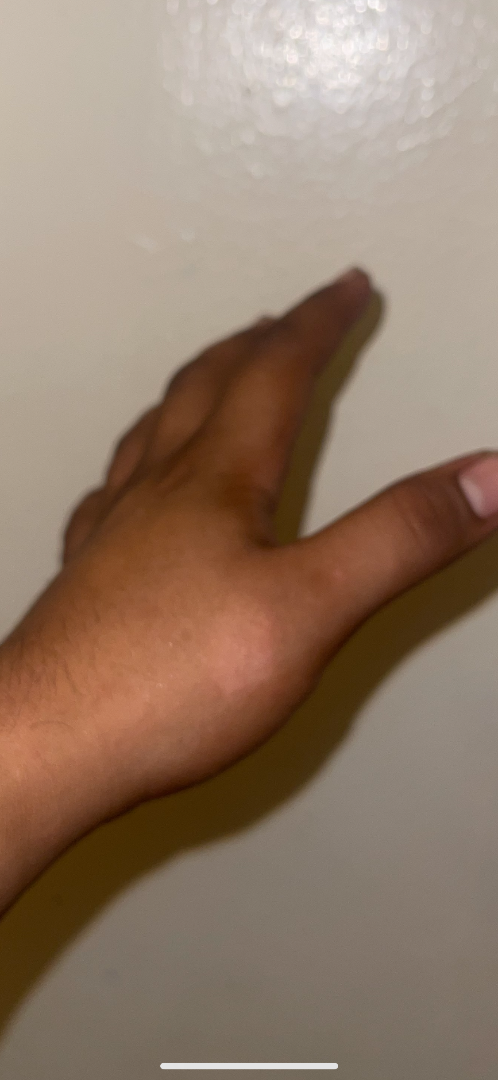assessment=not assessable; photo taken=close-up.